The leg is involved; this image was taken at an angle — 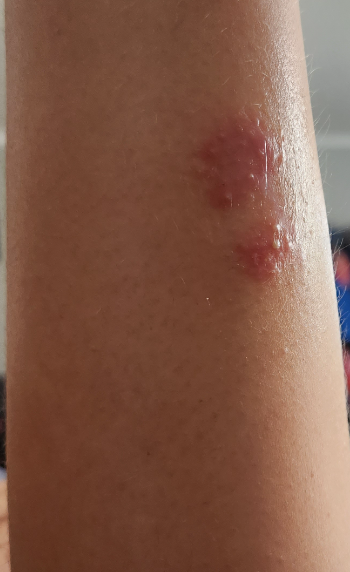assessment: indeterminate from the photograph